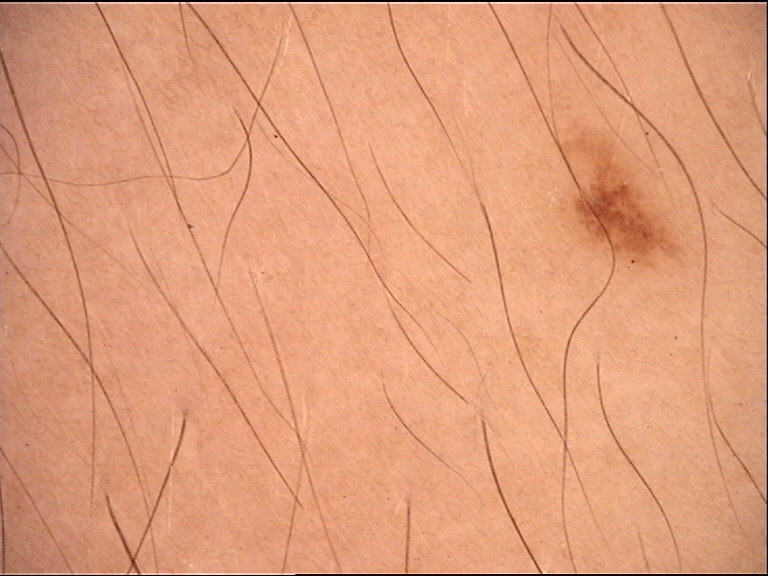<case>
  <diagnosis>
    <name>dysplastic junctional nevus</name>
    <code>jd</code>
    <malignancy>benign</malignancy>
    <super_class>melanocytic</super_class>
    <confirmation>expert consensus</confirmation>
  </diagnosis>
</case>